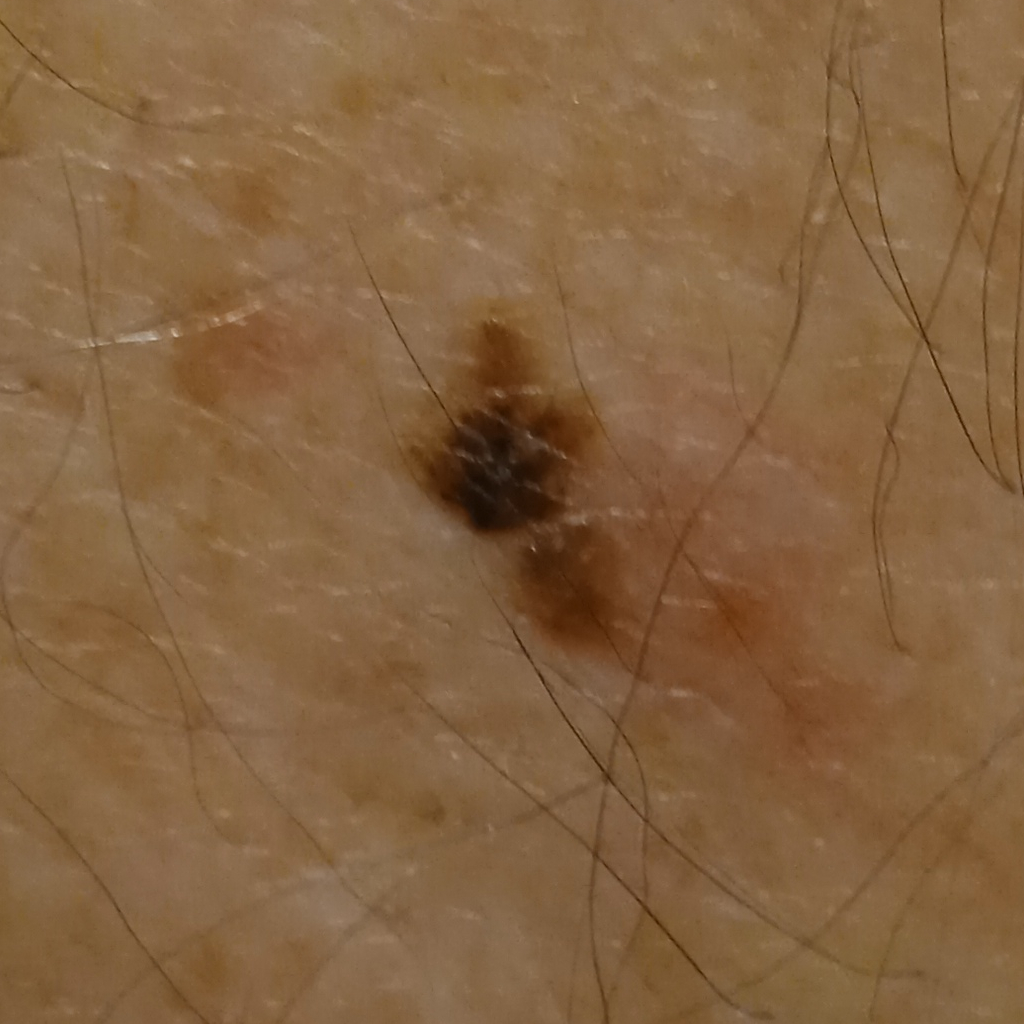Clinical context: The patient says their skin reddens with sun exposure. On a questionnaire the patient reported a personal history of skin cancer and a personal history of cancer. Collected as part of a research study, without a referral diagnosis. The patient describes having few moles overall. A clinical photograph of a skin lesion. A male subject 76 years of age. The lesion is located on the back. The lesion measures approximately 7.8 mm. Impression: The consensus diagnosis for this lesion was a seborrheic keratosis.